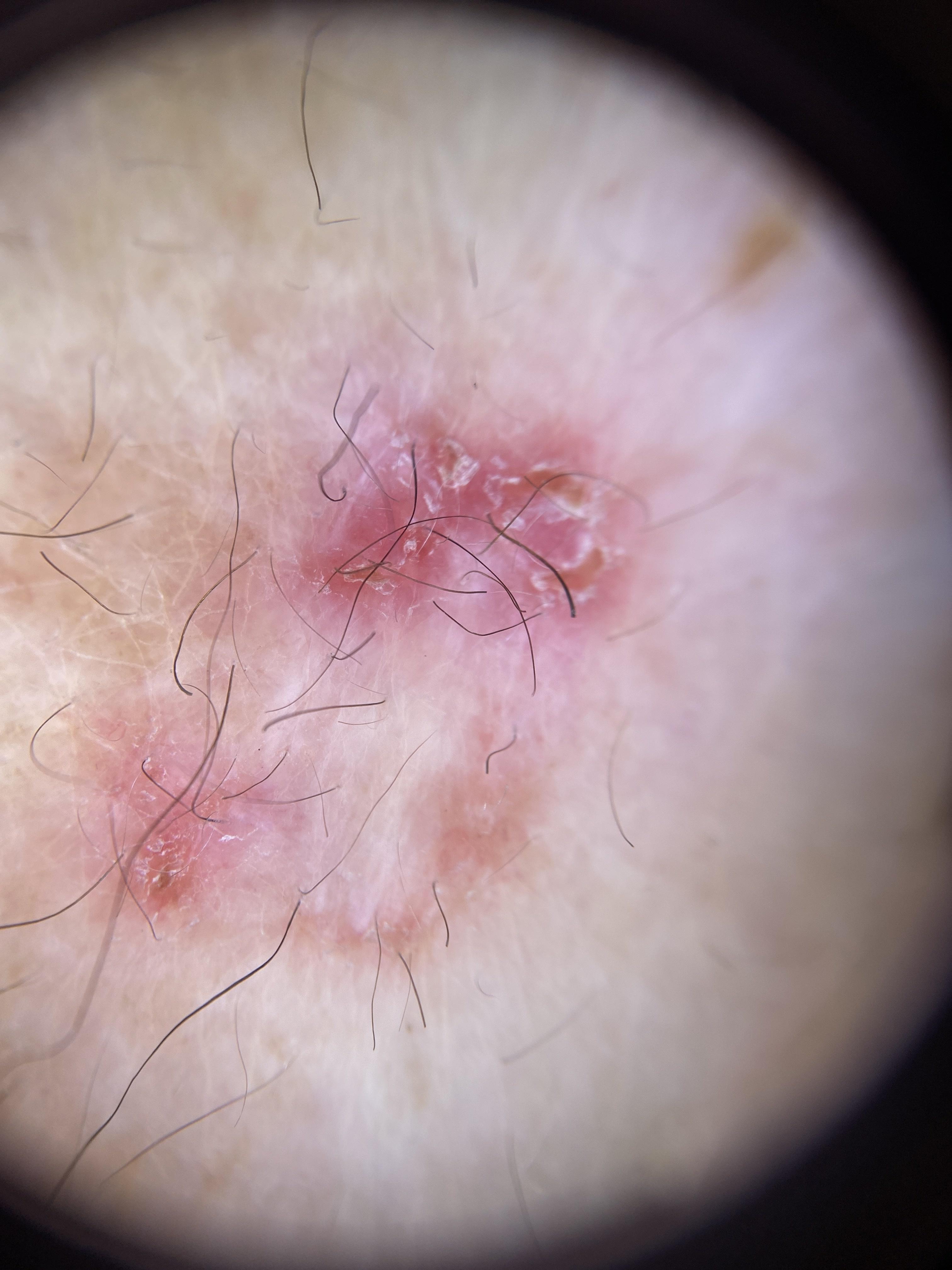Q: Patient demographics?
A: female, aged around 80
Q: How was this image acquired?
A: dermoscopic image
Q: What Fitzpatrick skin type was recorded?
A: II
Q: Where on the body is the lesion?
A: an upper extremity
Q: What is the diagnosis?
A: Basal cell carcinoma (biopsy-proven)